A skin lesion imaged with a dermatoscope:
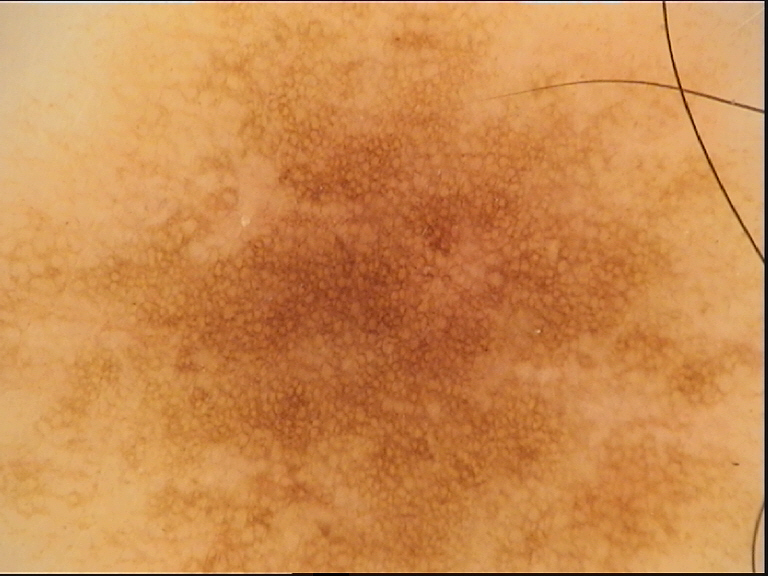Q: What is the diagnosis?
A: junctional nevus (expert consensus)